The affected area is the leg; a close-up photograph: 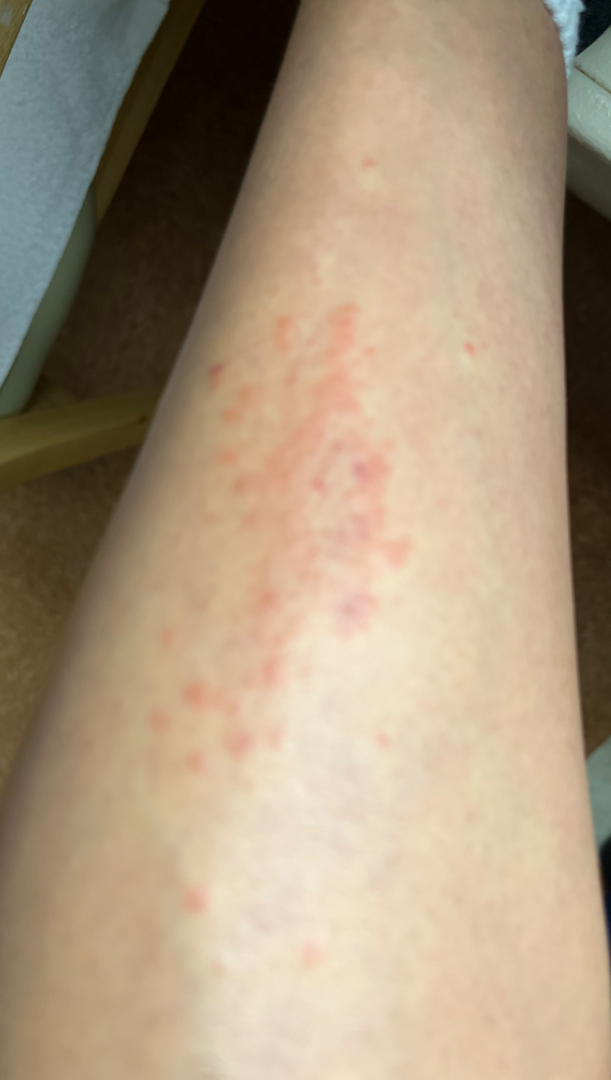Q: Could the case be diagnosed?
A: unable to determine